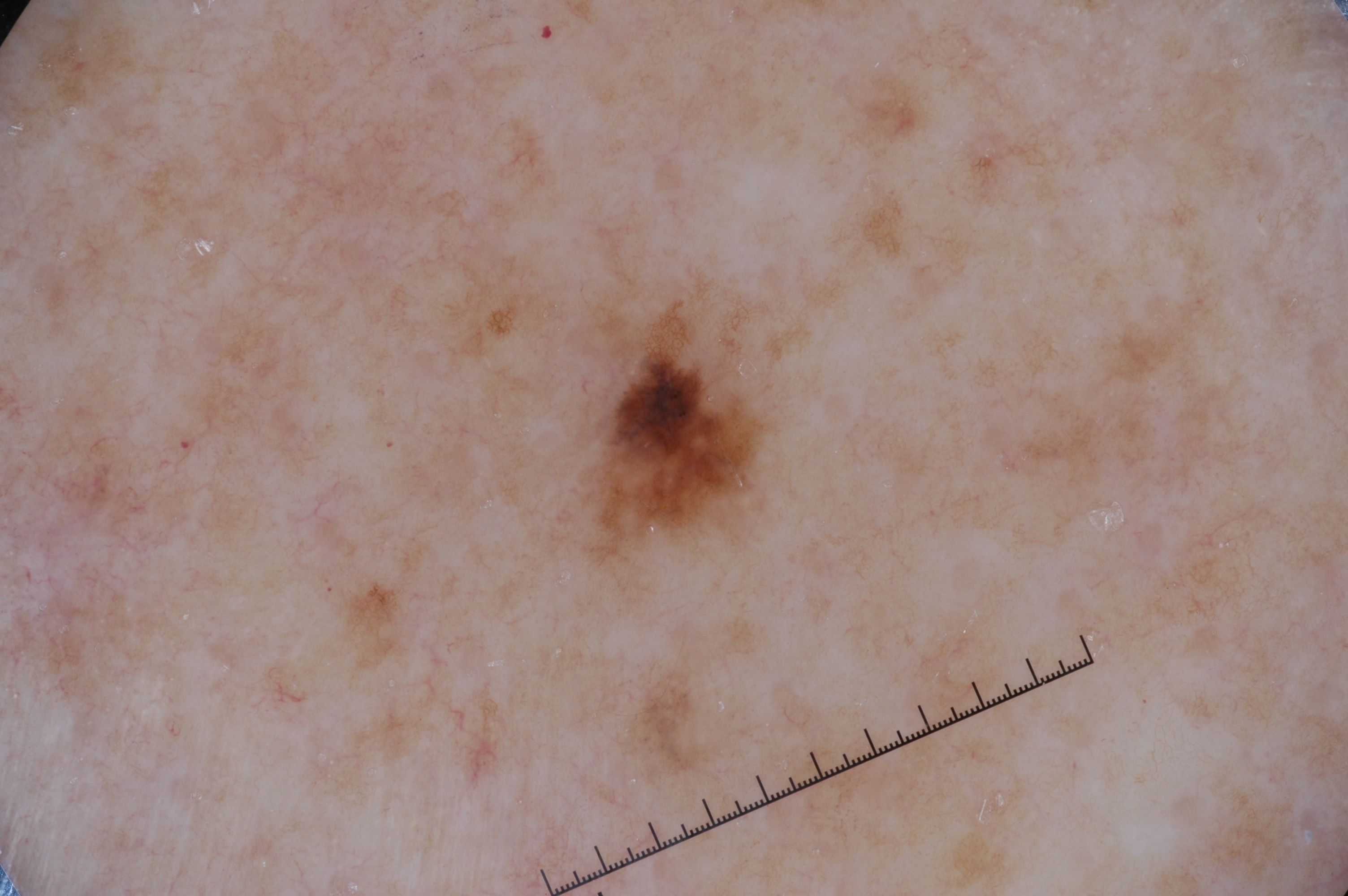The subject is a female roughly 50 years of age. A skin lesion imaged with a dermatoscope. A small lesion within a wider field of skin. The visible lesion spans 579/350/780/557. Dermoscopic assessment notes pigment network, with no milia-like cysts, negative network, or streaks. The lesion was assessed as a melanocytic nevus, a benign skin lesion.